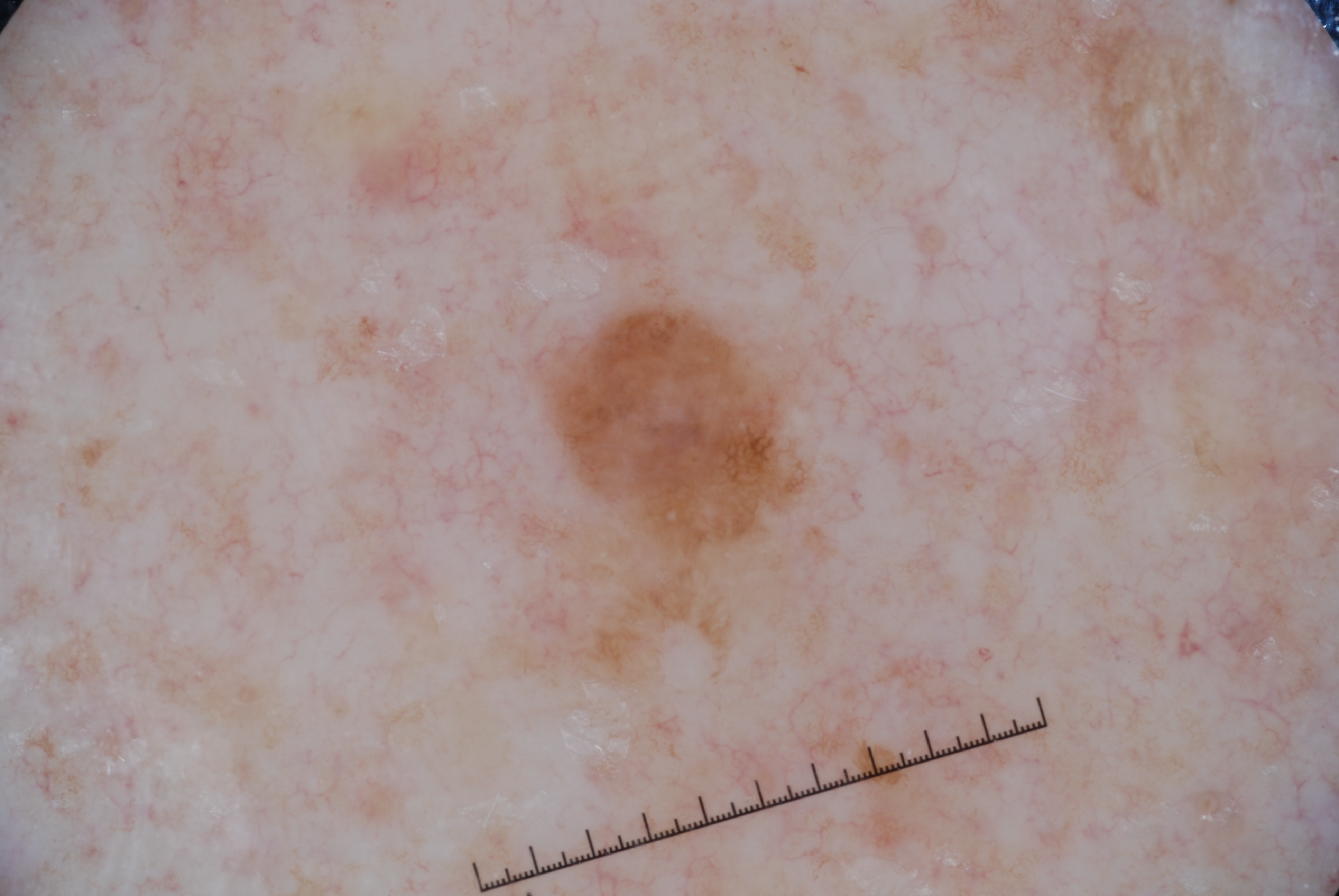This is a dermoscopic photograph of a skin lesion.
A male patient in their mid- to late 60s.
In (x1, y1, x2, y2) order, the lesion's extent is 480 271 830 706.
Dermoscopic review identifies pigment network, with no negative network, streaks, or milia-like cysts.
Clinically diagnosed as a melanocytic nevus.